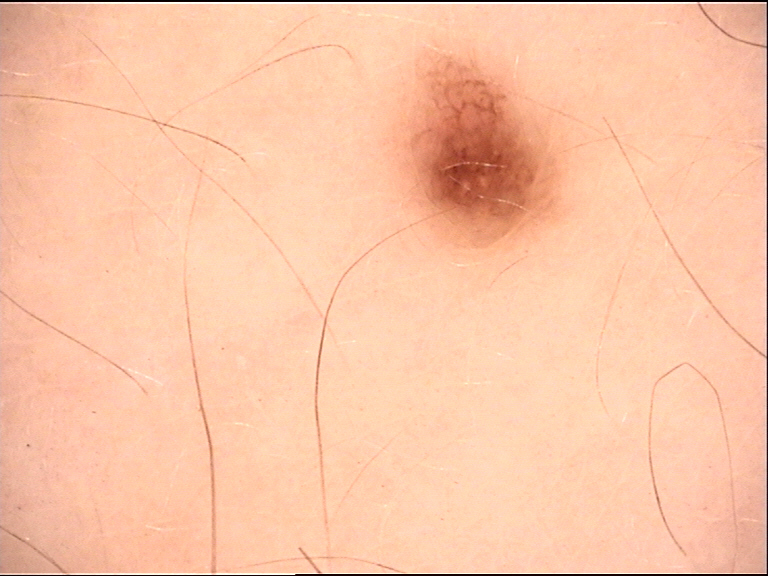Diagnosed as a benign lesion — a dysplastic junctional nevus.